Dermoscopy of a skin lesion:
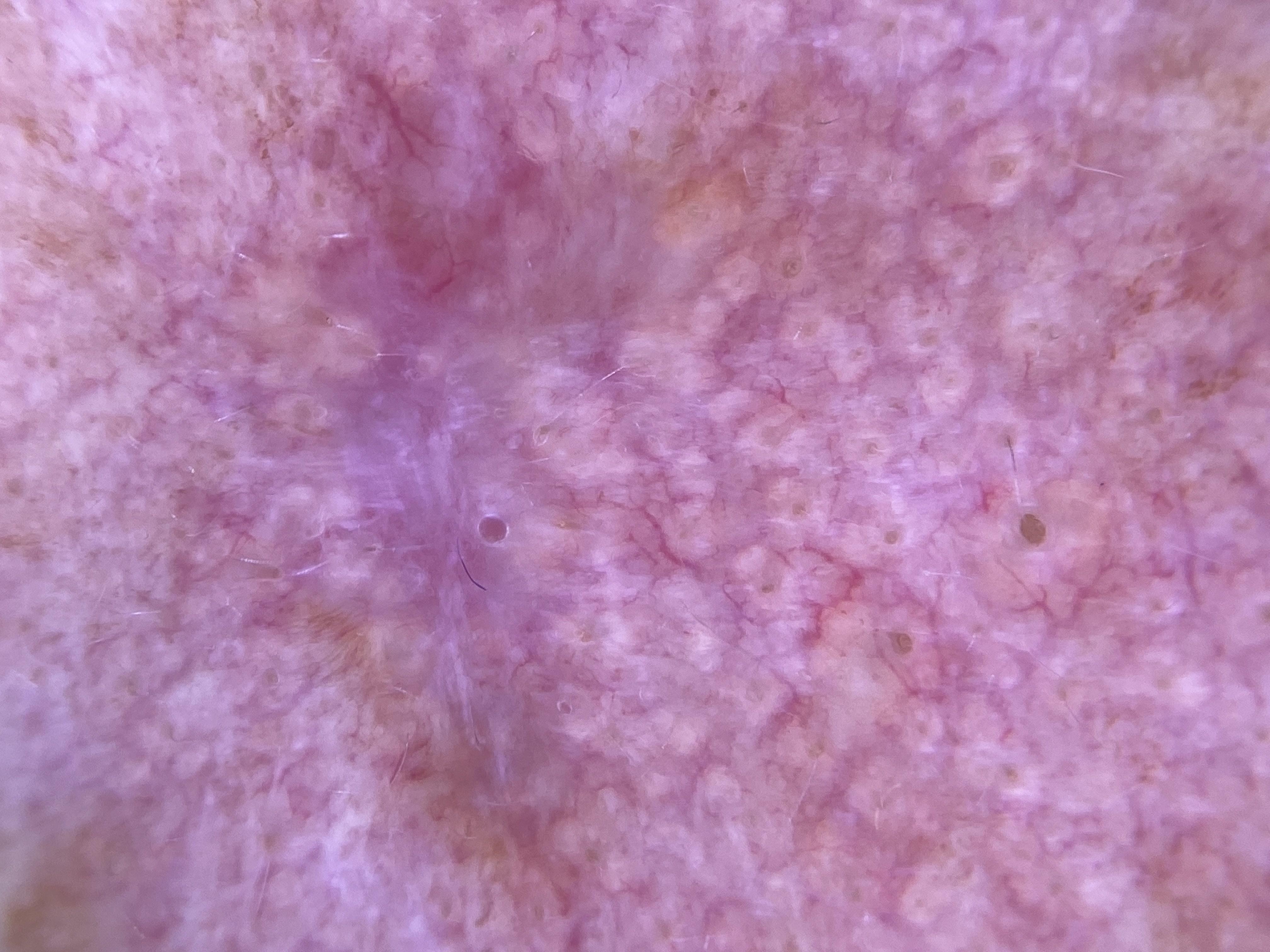pathology = Basal cell carcinoma (biopsy-proven).